The patient described the issue as skin that appeared healthy to them. An image taken at an angle. The leg is involved. Texture is reported as flat. The patient indicates associated fatigue. The condition has been present for less than one week. Female patient, age 50–59. No relevant lesion symptoms reported.
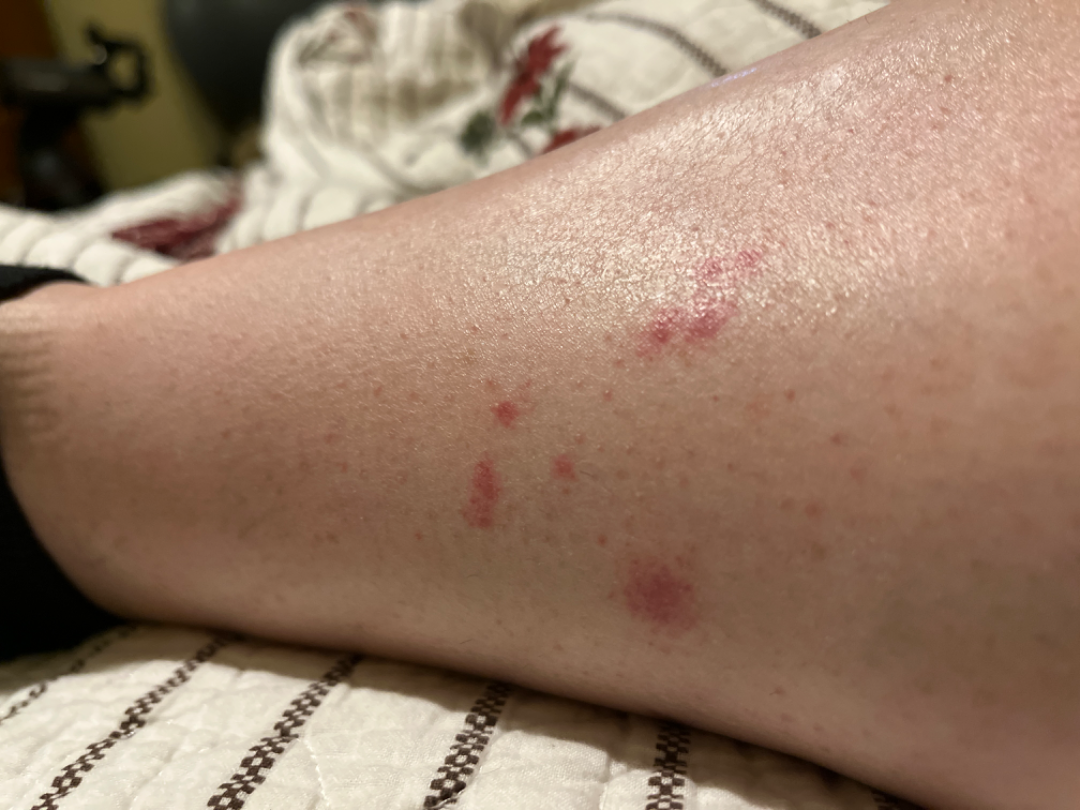On dermatologist assessment of the image: the leading consideration is Pigmented purpuric eruption; also consider Insect Bite; less likely is Allergic Contact Dermatitis; less probable is Purpura.